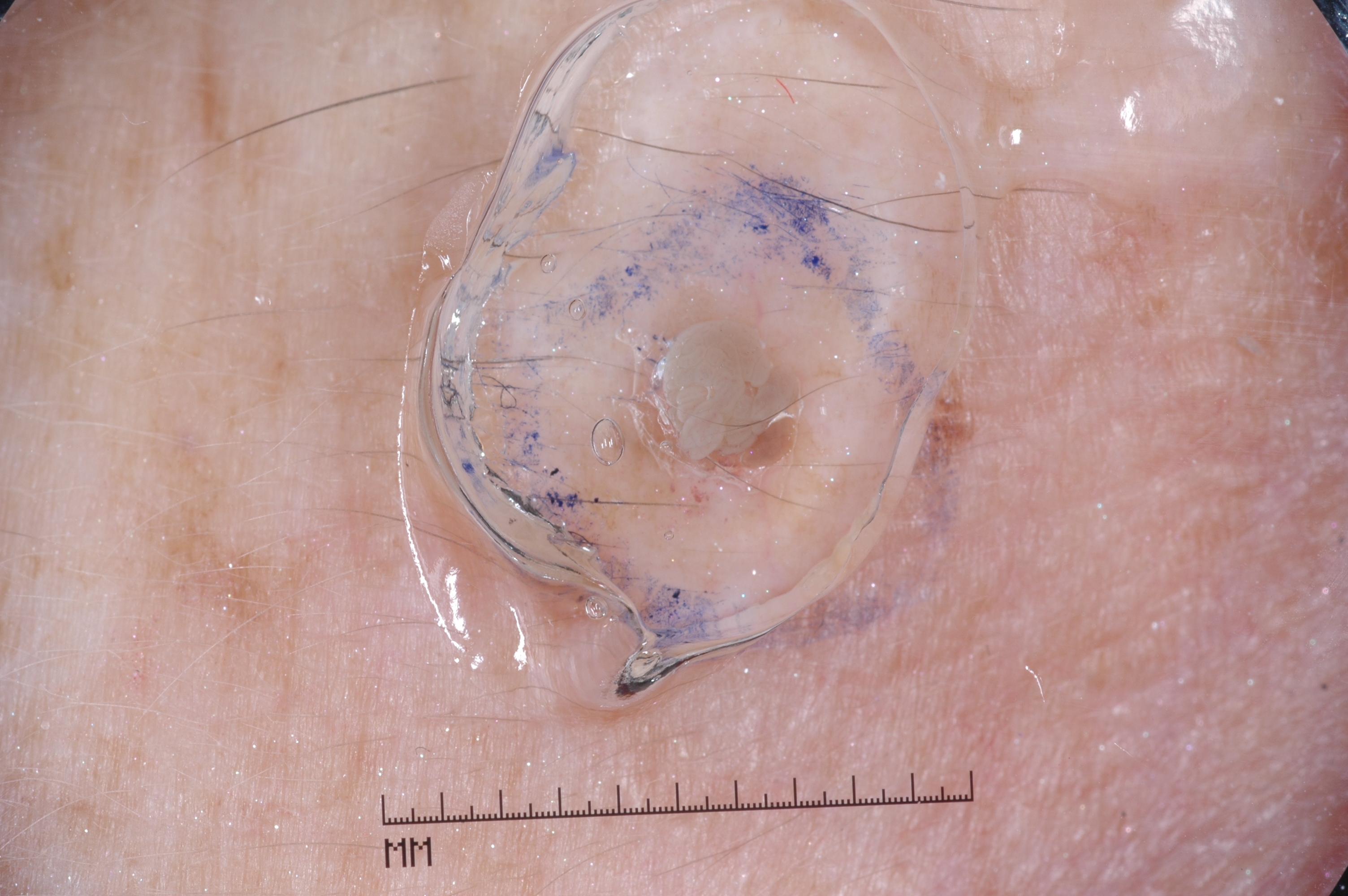A female patient, roughly 60 years of age.
A dermoscopy image of a single skin lesion.
Dermoscopic assessment notes no pigment network, milia-like cysts, streaks, or negative network.
In (x1, y1, x2, y2) order, the lesion occupies the region <box>623, 286, 813, 489</box>.
A small lesion occupying a minor part of the field.
Consistent with a seborrheic keratosis, a benign lesion.